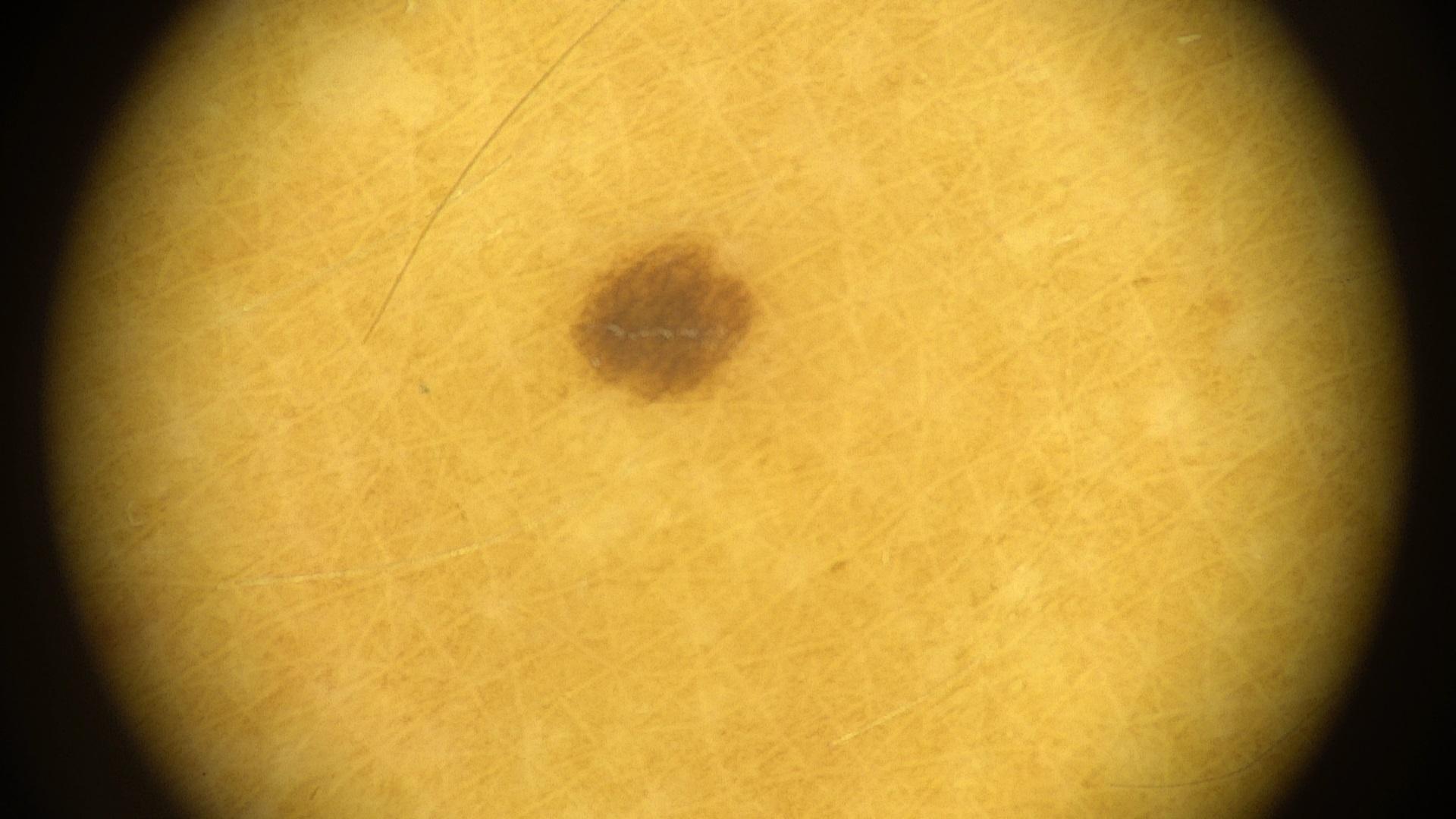imaging = contact-polarized dermoscopy
subject = female, approximately 35 years of age
site = an upper extremity
diagnostic label = Nevus (clinical impression)